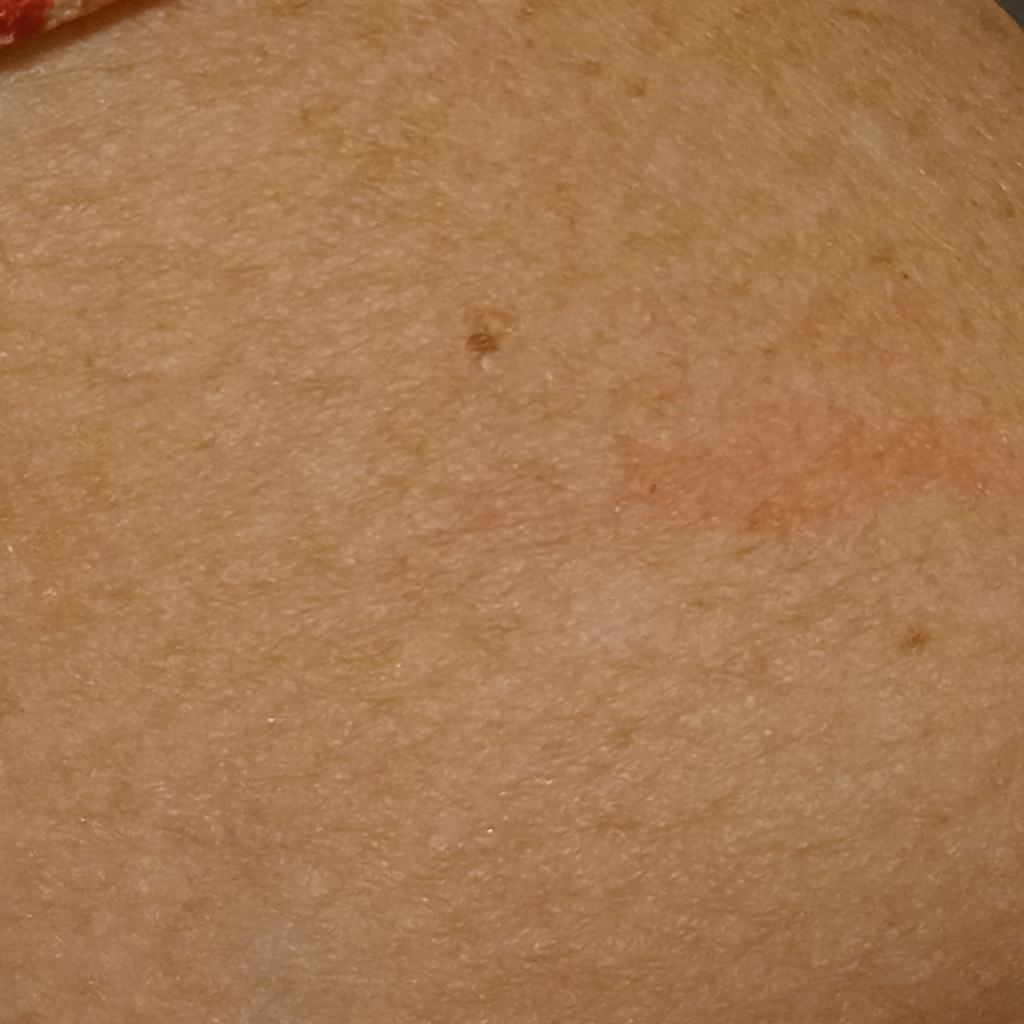risk factors = a personal history of skin cancer
sun reaction = skin reddens with sun exposure
assessment = melanocytic nevus (dermatologist consensus)